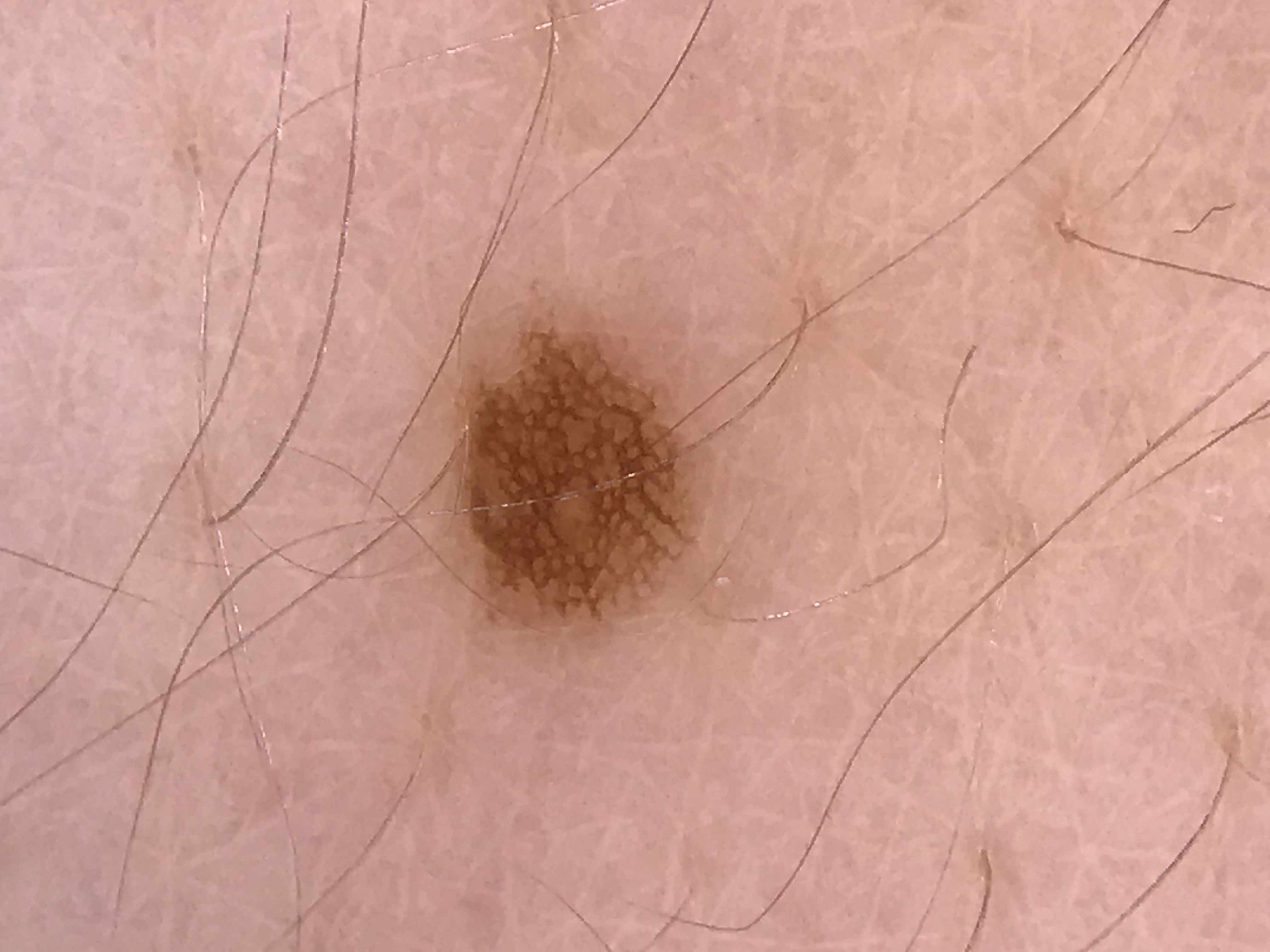Impression: The diagnosis was a banal lesion — a junctional nevus.